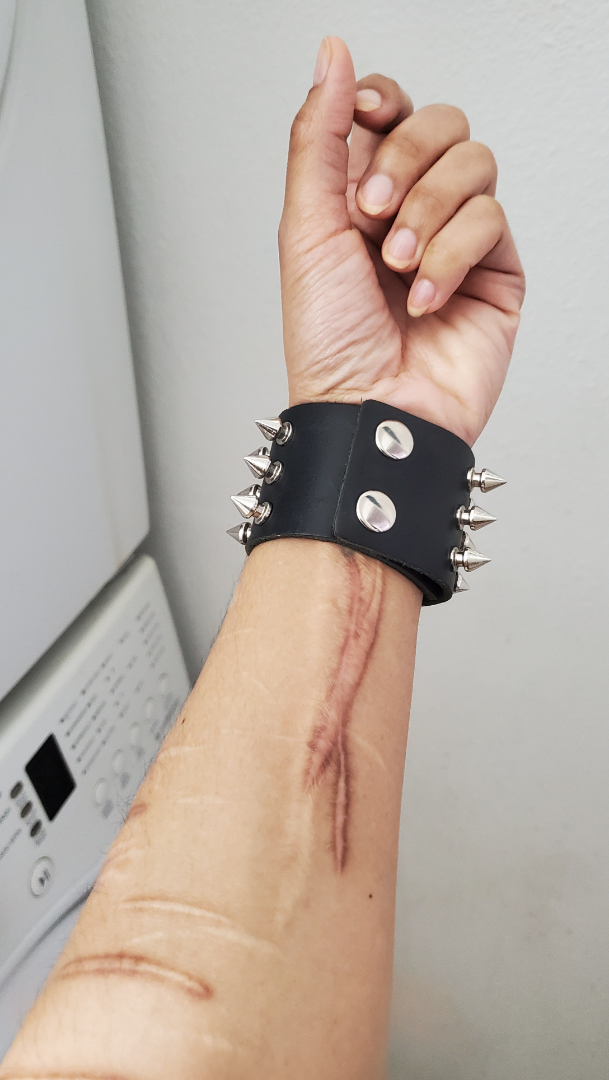History:
The patient indicates the lesion is raised or bumpy. The photograph was taken at a distance. The affected area is the arm. No relevant lesion symptoms reported. The condition has been present for more than five years. Skin tone: Fitzpatrick phototype III; human graders estimated MST 3 or 4 (two reviewer pools).
Impression:
On independent review by the dermatologists: consistent with Scar Condition.